The patient was assessed as skin type II; a male patient age 50: 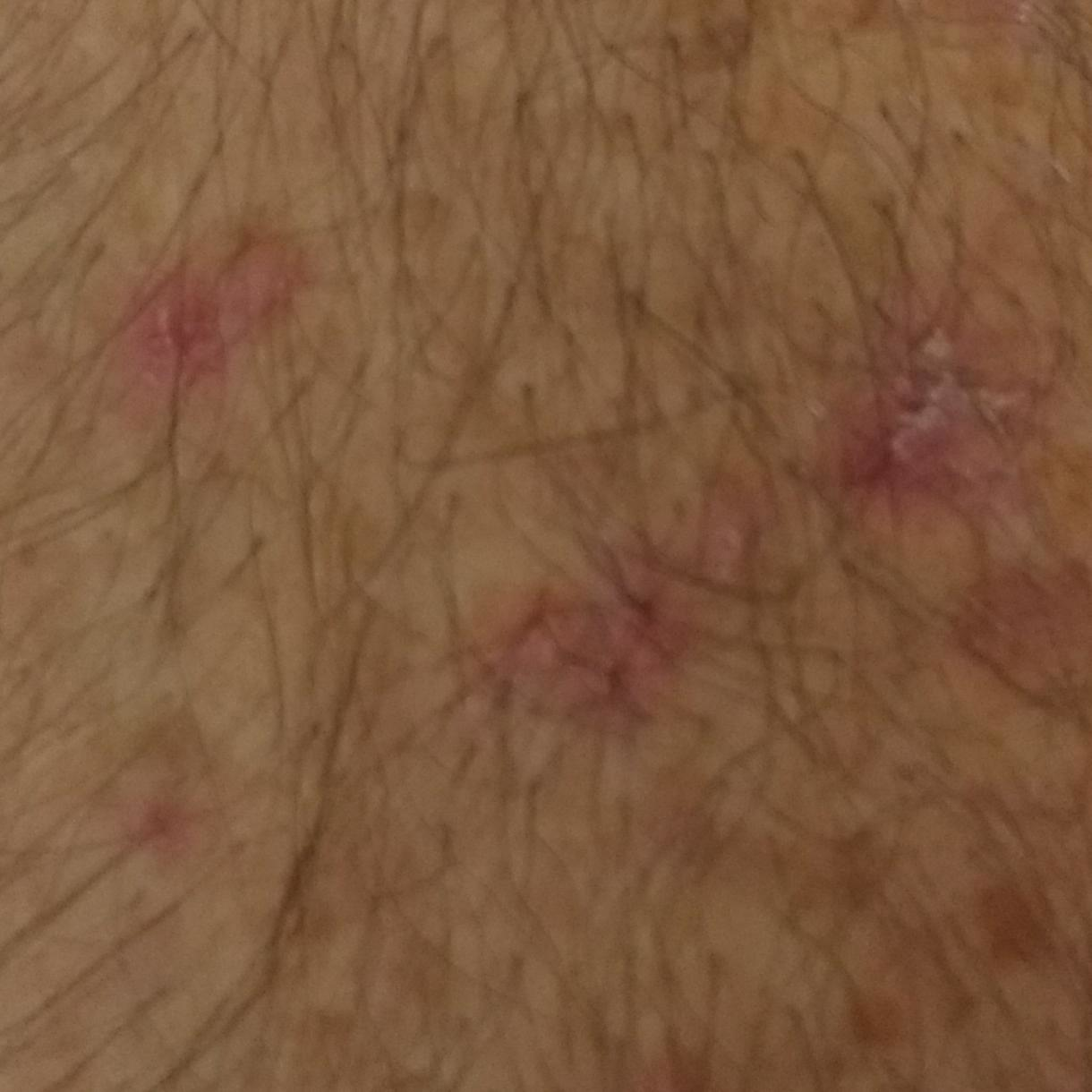Findings: The lesion is on a forearm. The lesion measures 9 × 6 mm. The patient describes that the lesion itches. Conclusion: The clinical impression was a lesion of indeterminate malignant potential — an actinic keratosis.